A male patient aged around 75 · a dermatoscopic image of a skin lesion:
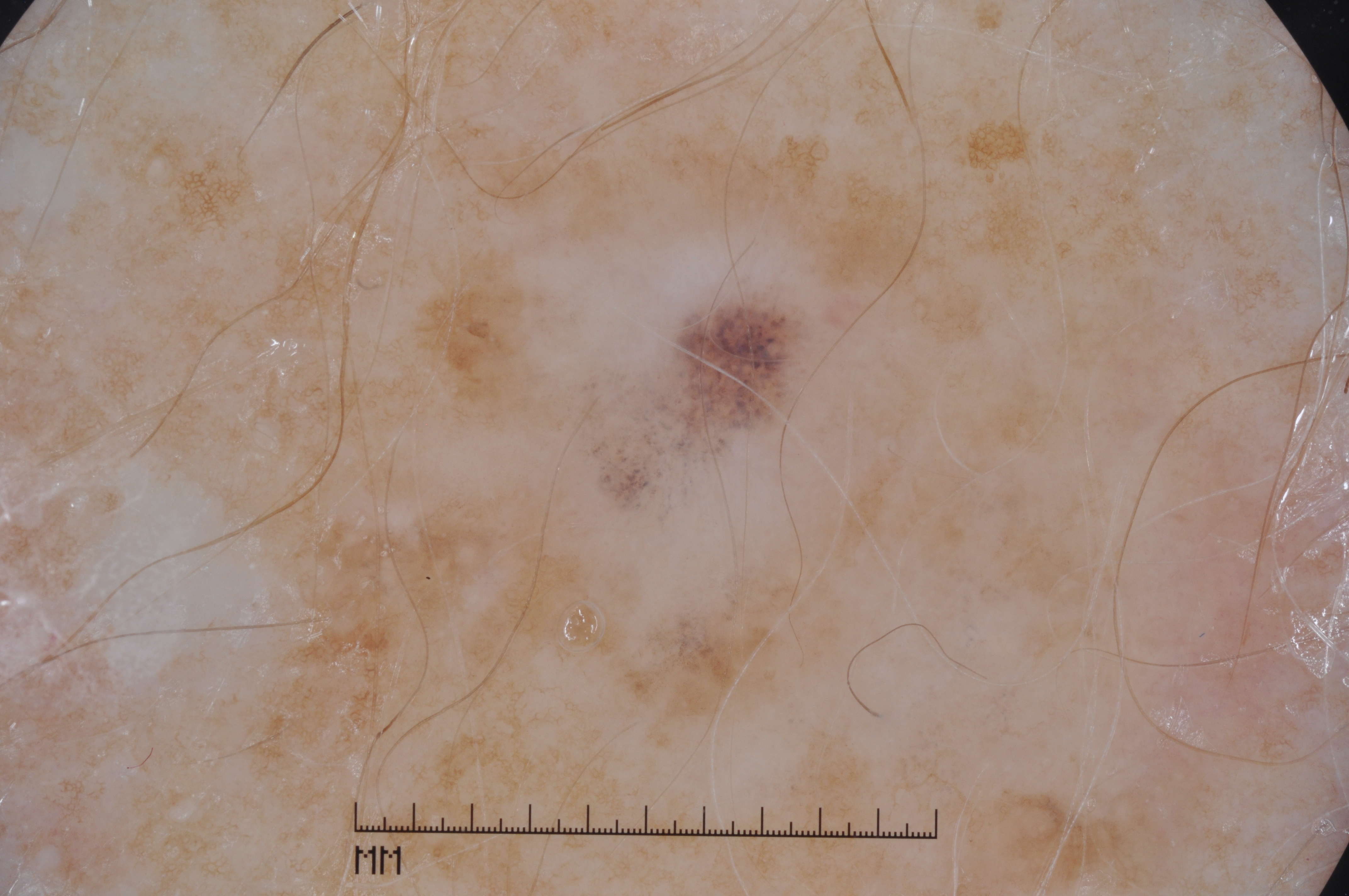location — x1=550, y1=268, x2=817, y2=535
dermoscopic features not present — streaks, pigment network, milia-like cysts, and negative network
diagnostic label — a melanoma